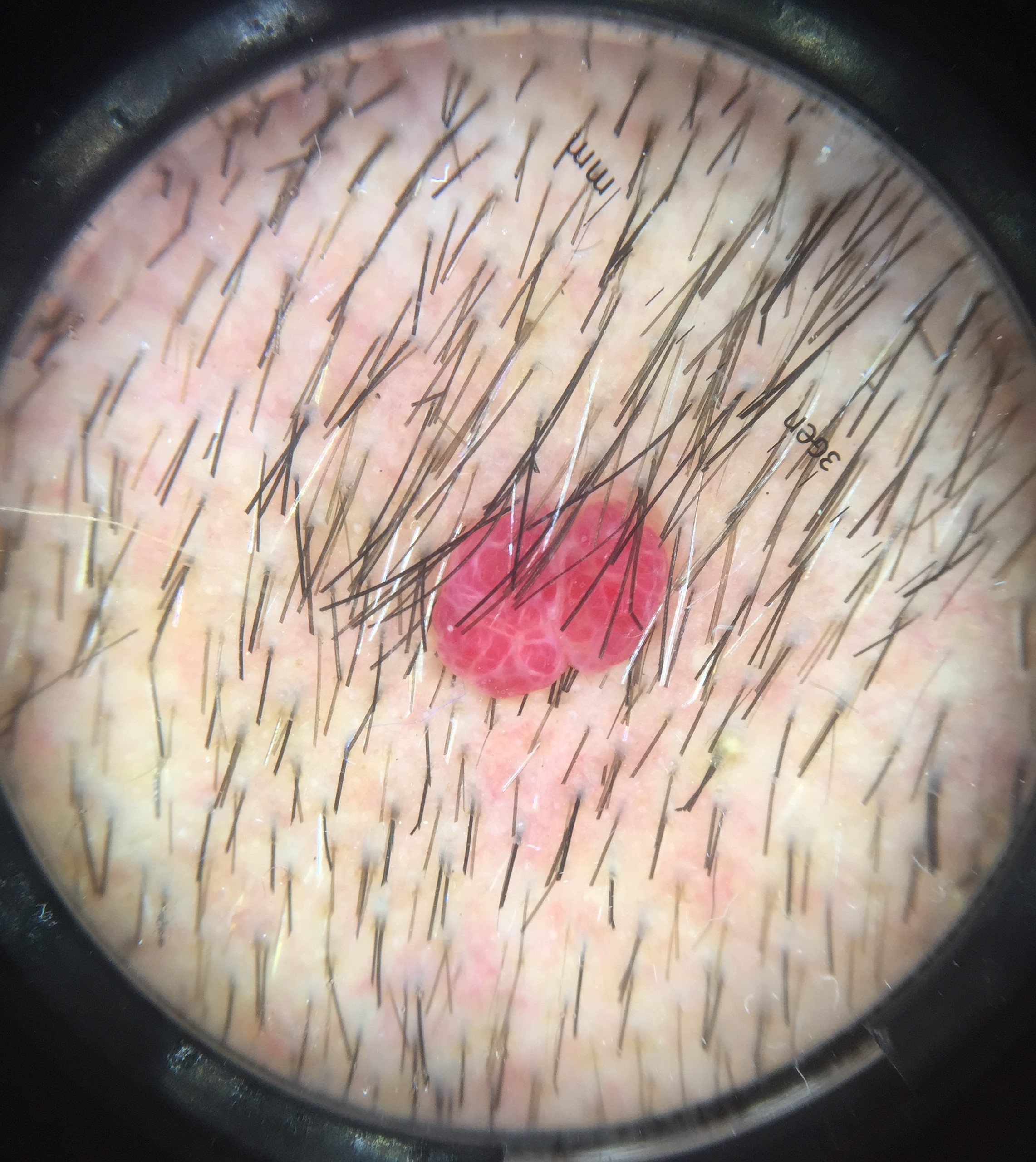Findings: A dermoscopic image of a skin lesion. The architecture is that of a vascular lesion. Impression: The diagnostic label was a benign lesion — a hemangioma.